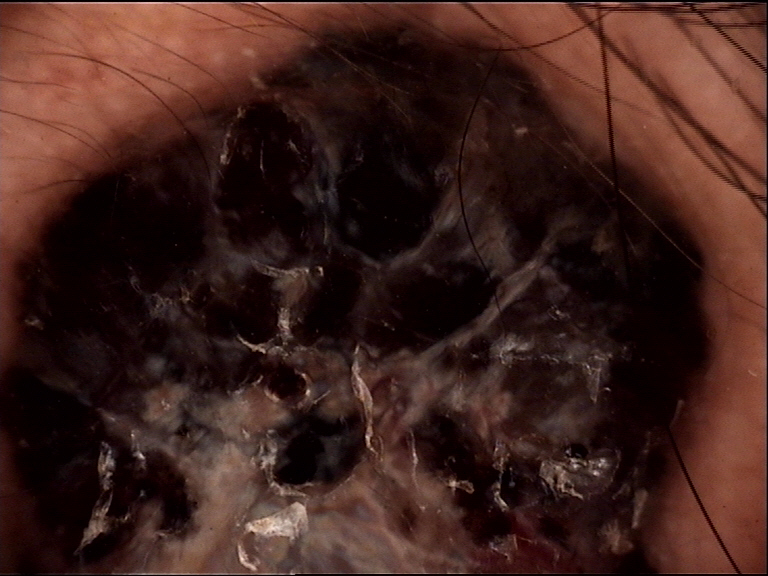Q: What did the workup show?
A: melanoma (biopsy-proven)